A female patient approximately 55 years of age. Dermoscopy of a skin lesion — 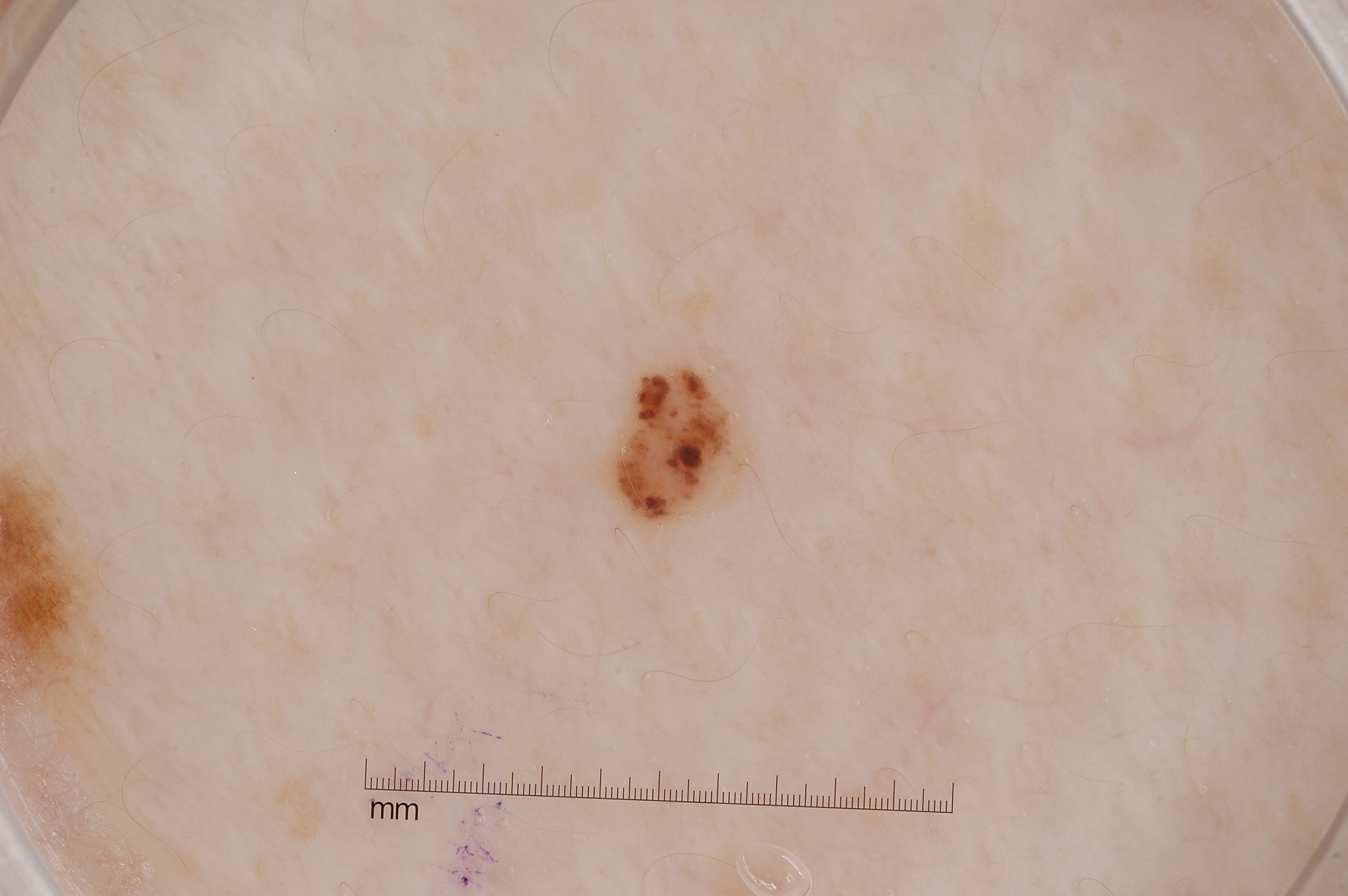Summary: Dermoscopic review identifies no negative network, milia-like cysts, streaks, or pigment network. The lesion's extent is box(611, 371, 737, 518). Conclusion: Clinically diagnosed as a melanocytic nevus, a benign skin lesion.